A dermatoscopic image of a skin lesion:
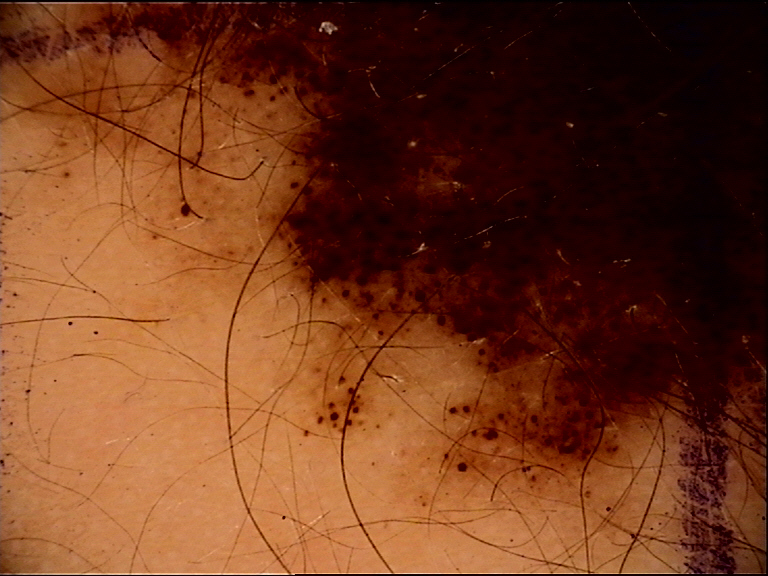{
  "lesion_type": {
    "main_class": "banal",
    "pattern": "compound"
  },
  "diagnosis": {
    "name": "congenital compound nevus",
    "code": "ccb",
    "malignancy": "benign",
    "super_class": "melanocytic",
    "confirmation": "expert consensus"
  }
}